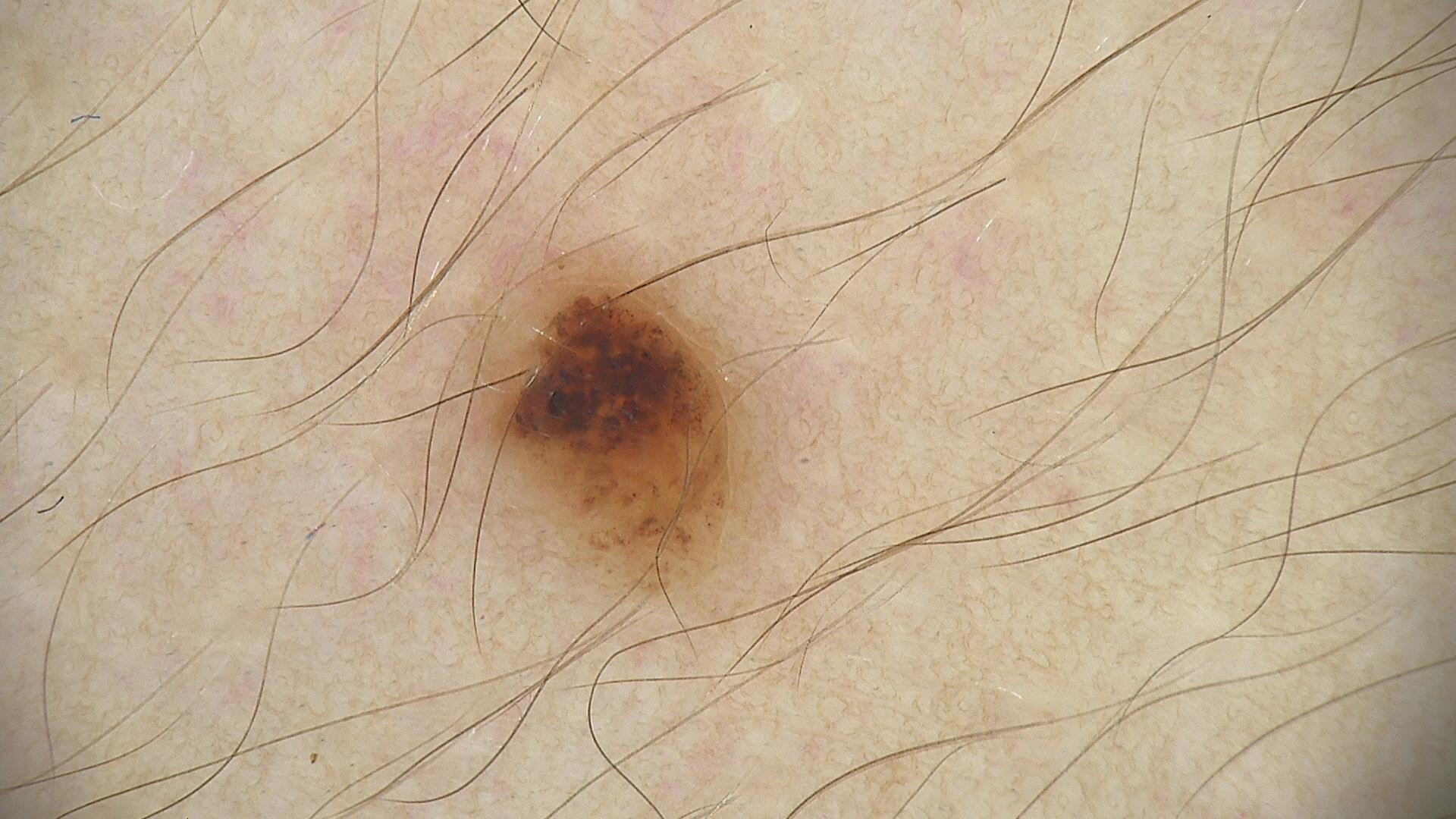A dermoscopic image of a skin lesion. The morphology is that of a banal lesion. Consistent with a compound nevus.